A skin lesion imaged with a dermatoscope.
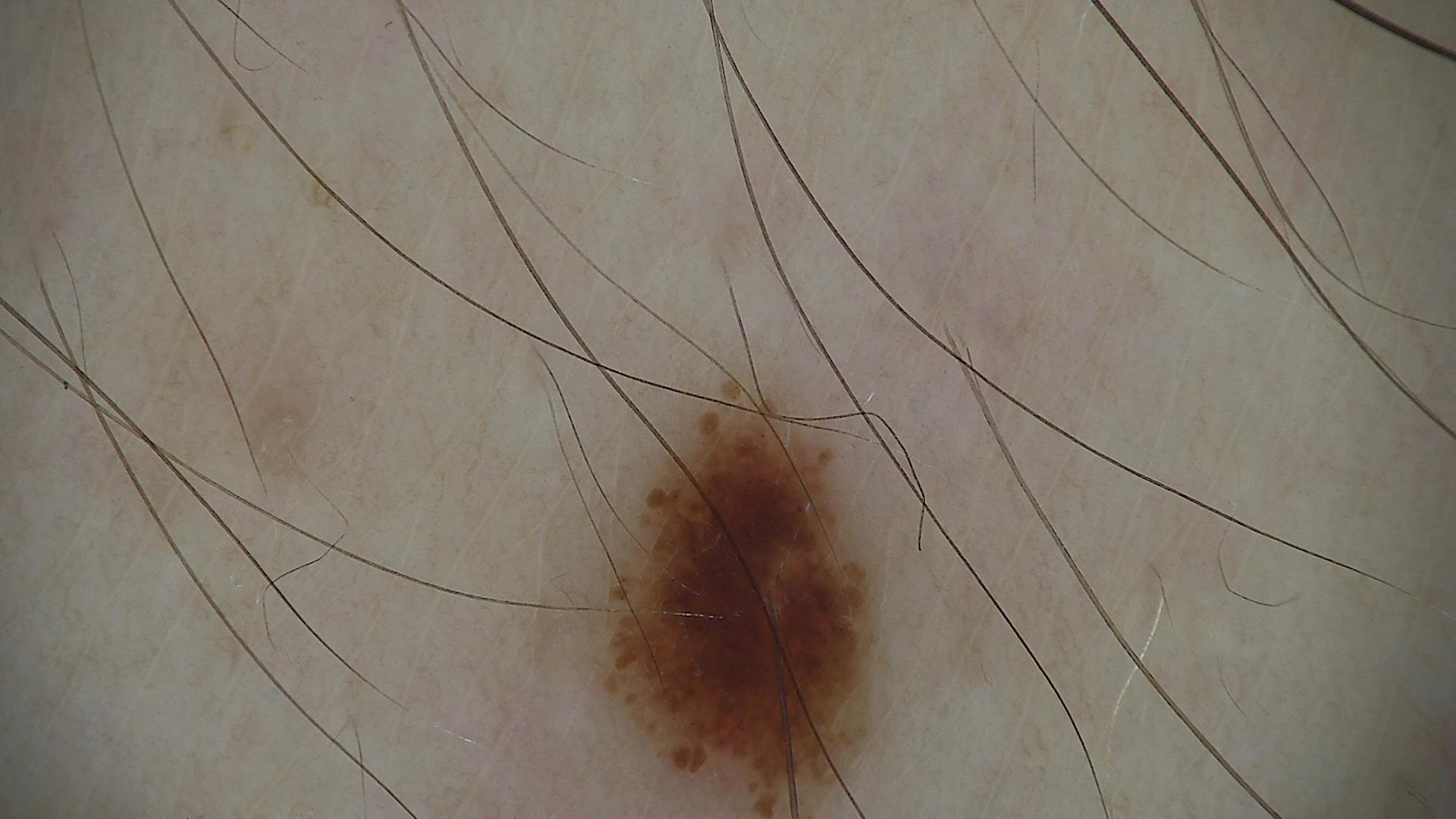Consistent with a benign lesion — a dysplastic junctional nevus.